The patient says their skin reddens with sun exposure; the patient describes having a moderate number of moles; acquired for a research image collection, with no referral diagnosis; a female subject 27 years of age: 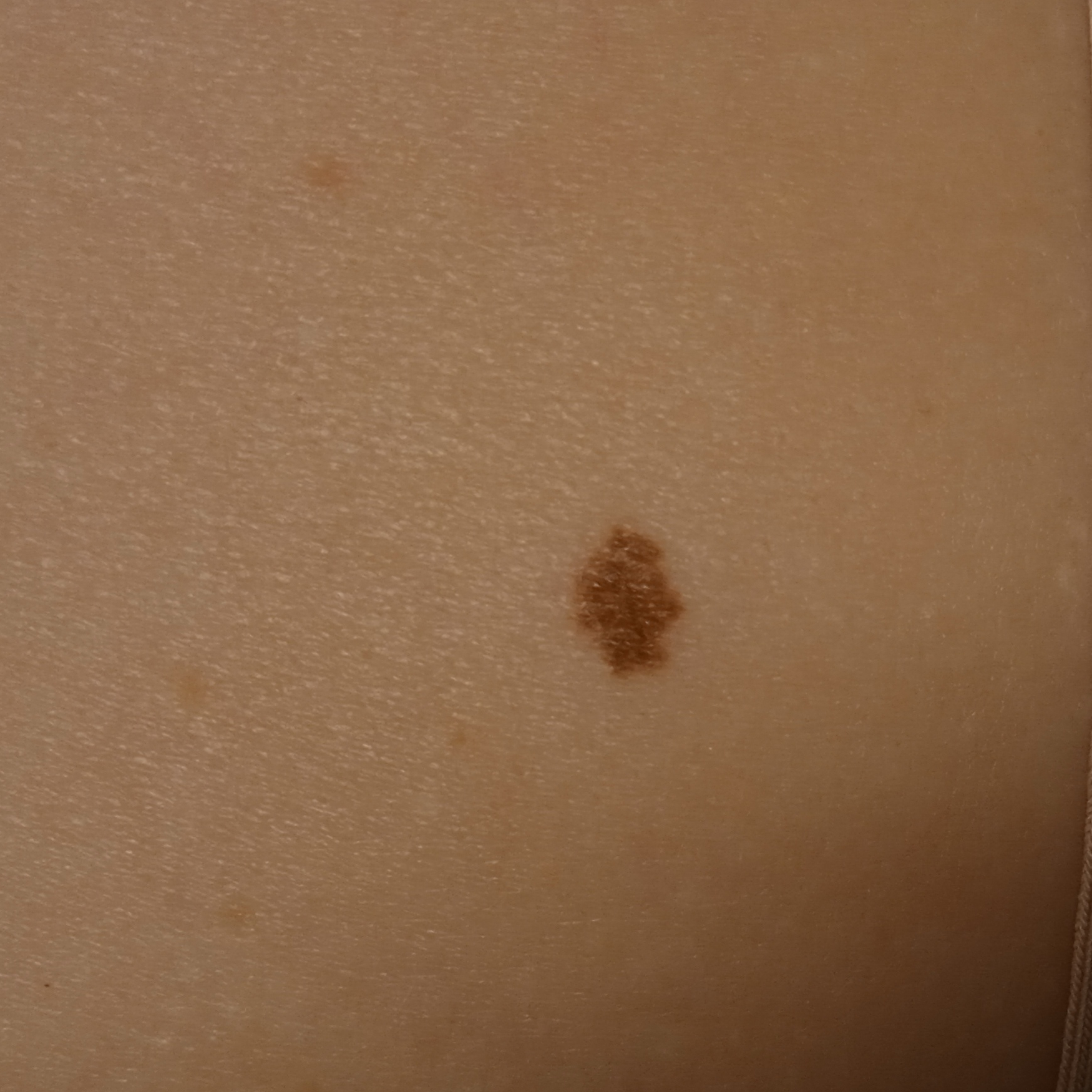Findings:
- location: an arm
- diagnostic label: atypical (dysplastic) nevus — dermatologist consensus